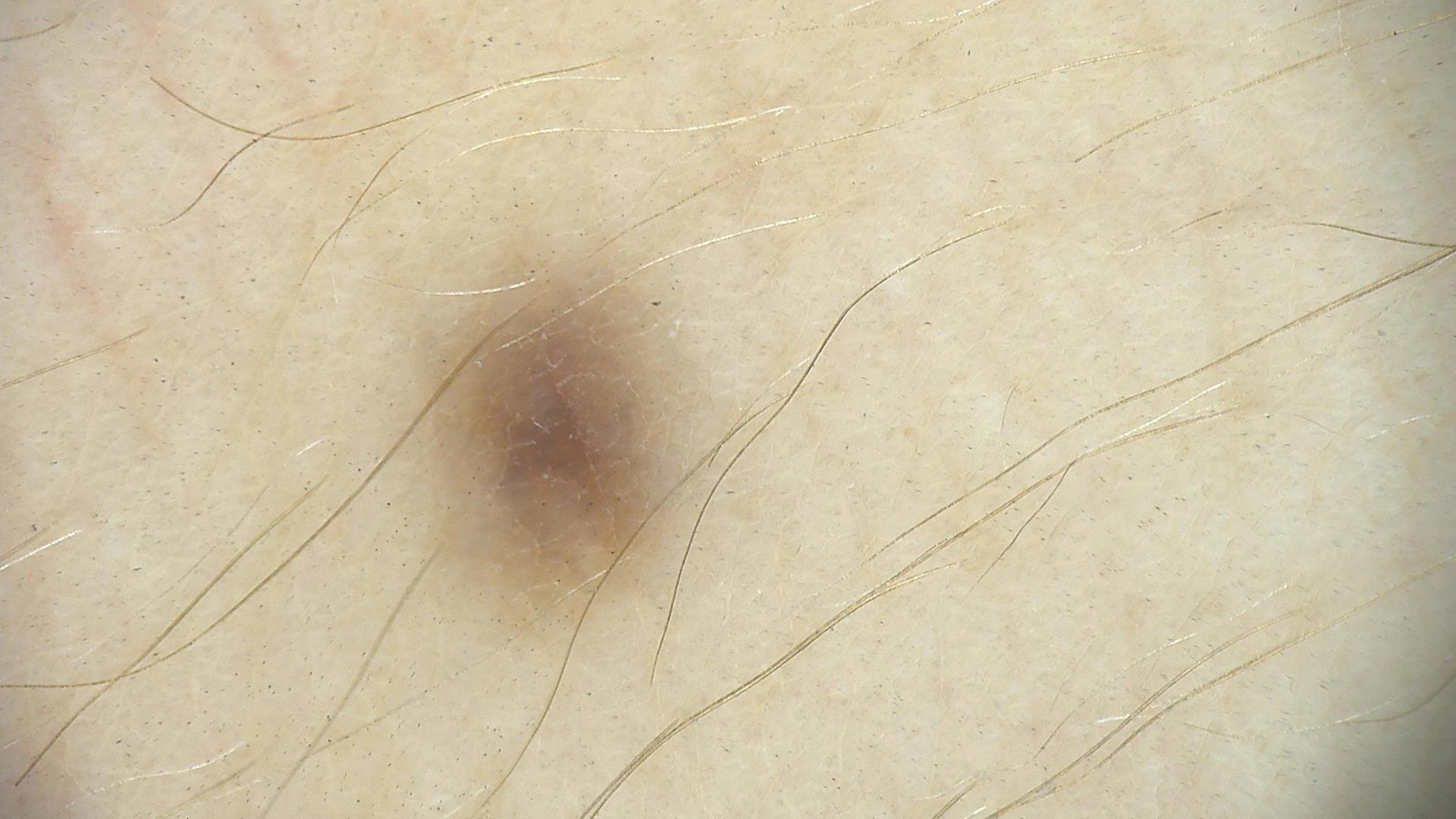The diagnosis was a blue nevus.